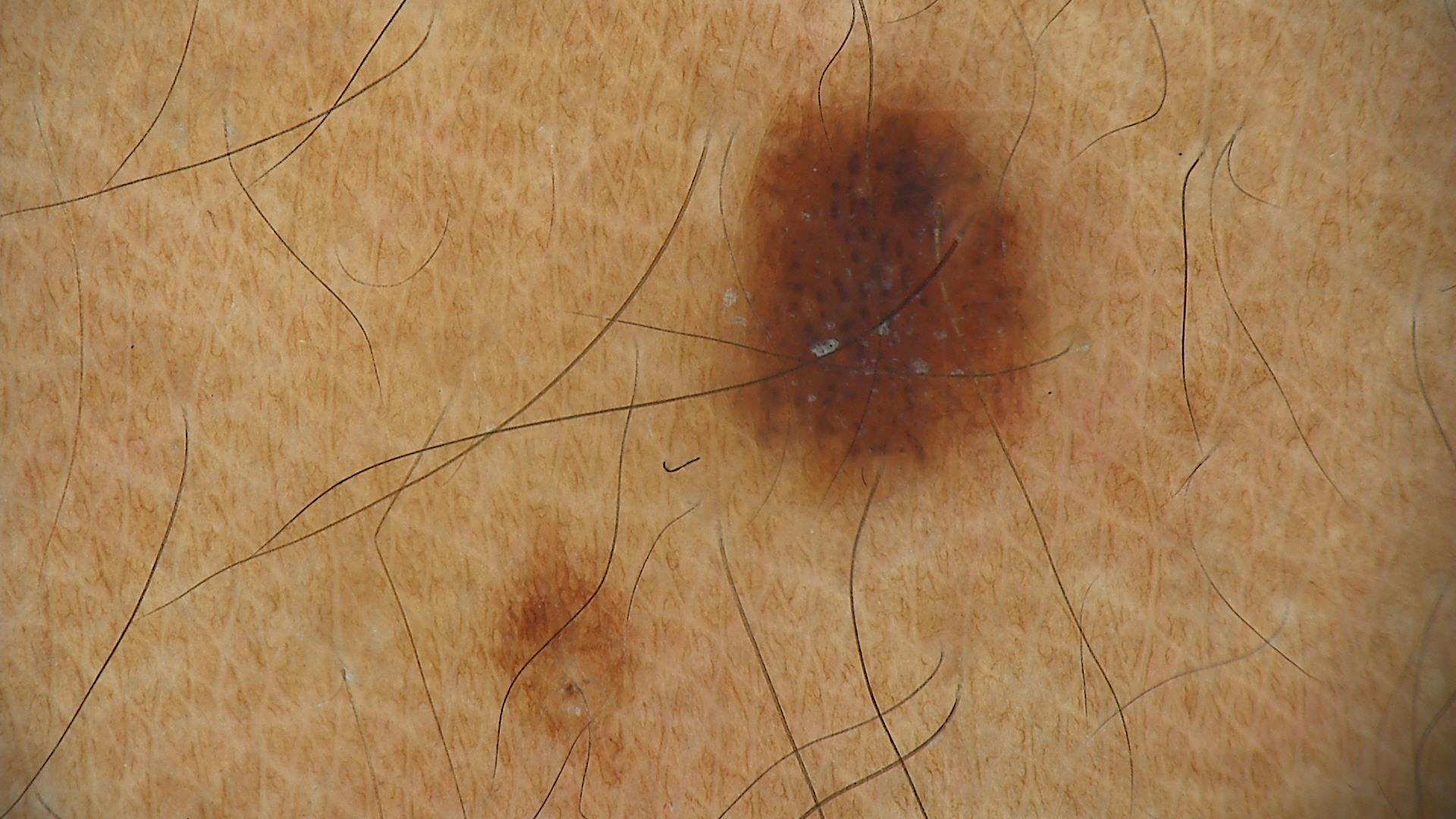• class — compound nevus (expert consensus)